The chart notes prior malignancy (patient or family) and no alcohol use; a female patient aged 66; a clinical photo of a skin lesion taken with a smartphone; recorded as skin type II: 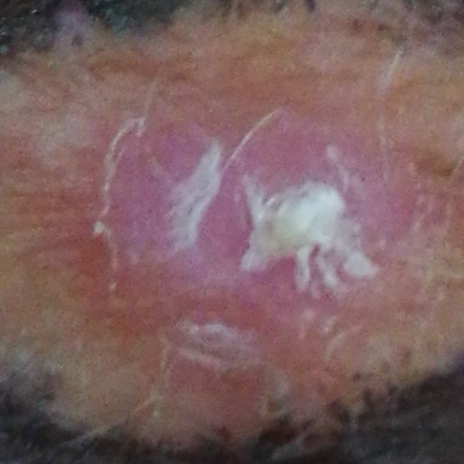  lesion_location: an arm
  symptoms:
    present:
      - itching
      - elevation
      - pain
  diagnosis:
    name: actinic keratosis
    code: ACK
    malignancy: indeterminate
    confirmation: histopathology